The patient did not report lesion symptoms; reported duration is one to four weeks; the photo was captured at an angle; the lesion involves the head or neck; the subject is 18–29, male; self-categorized by the patient as a rash; the contributor notes the lesion is fluid-filled.
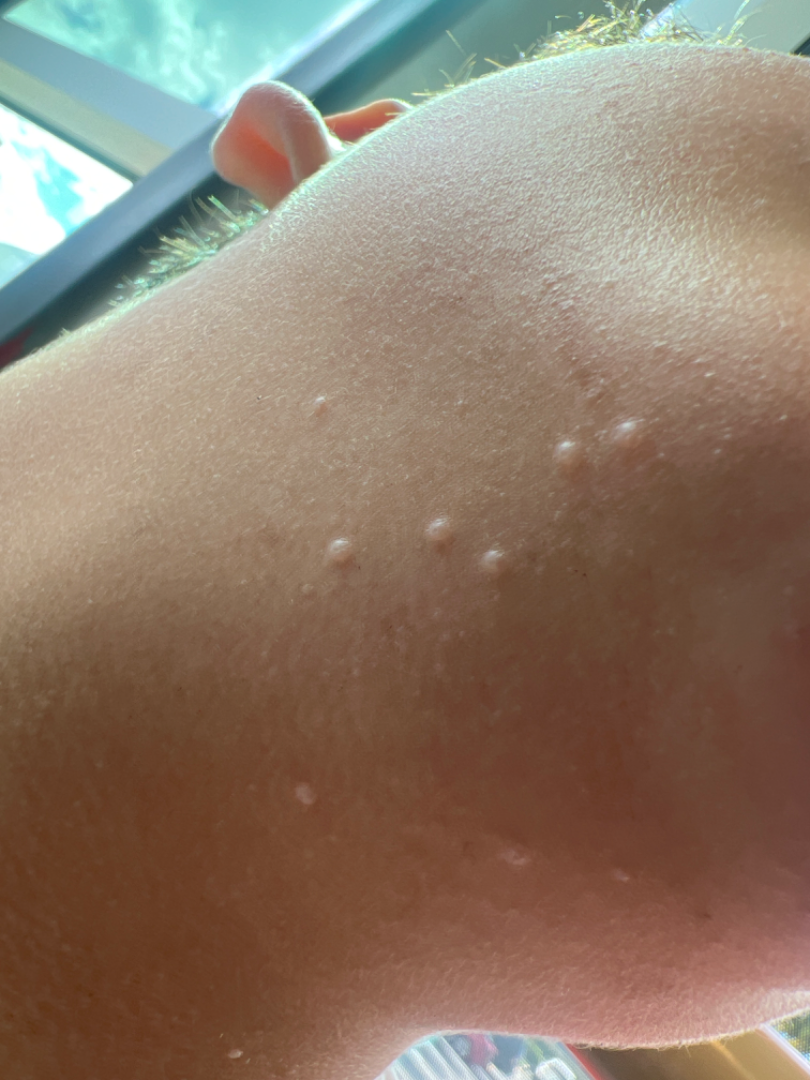The dermatologist could not determine a likely condition from the photograph alone.